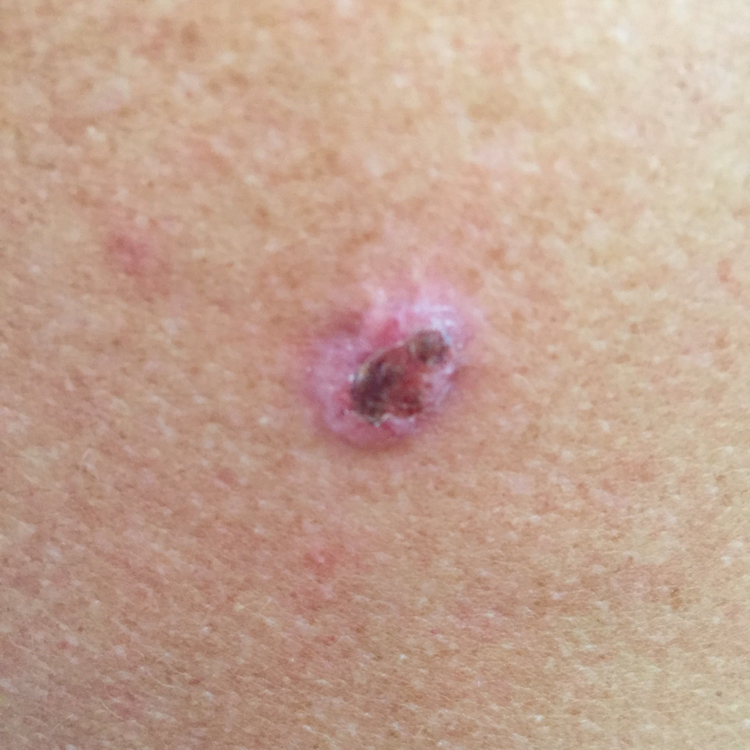The chart records pesticide exposure, alcohol use, and no prior skin cancer (patient or family). Recorded as skin type II. A clinical photograph of a skin lesion. The lesion is roughly 15 by 11 mm. Histopathology confirmed a basal cell carcinoma.